Associated systemic symptoms include fever; the photograph is a close-up of the affected area; present for one to four weeks; the lesion involves the back of the torso; skin tone: Fitzpatrick III; female patient, age 18–29 — 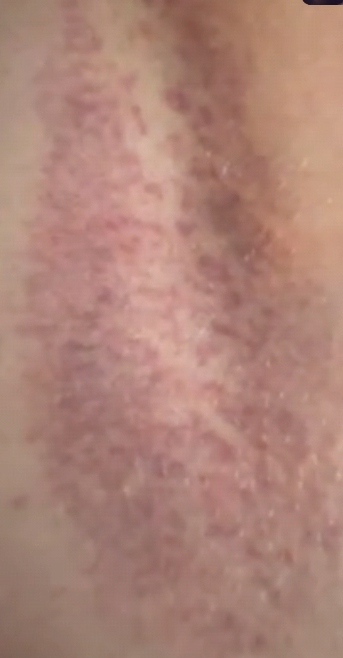{"assessment": "unable to determine"}